The patient is a female aged 50–59 · close-up view: 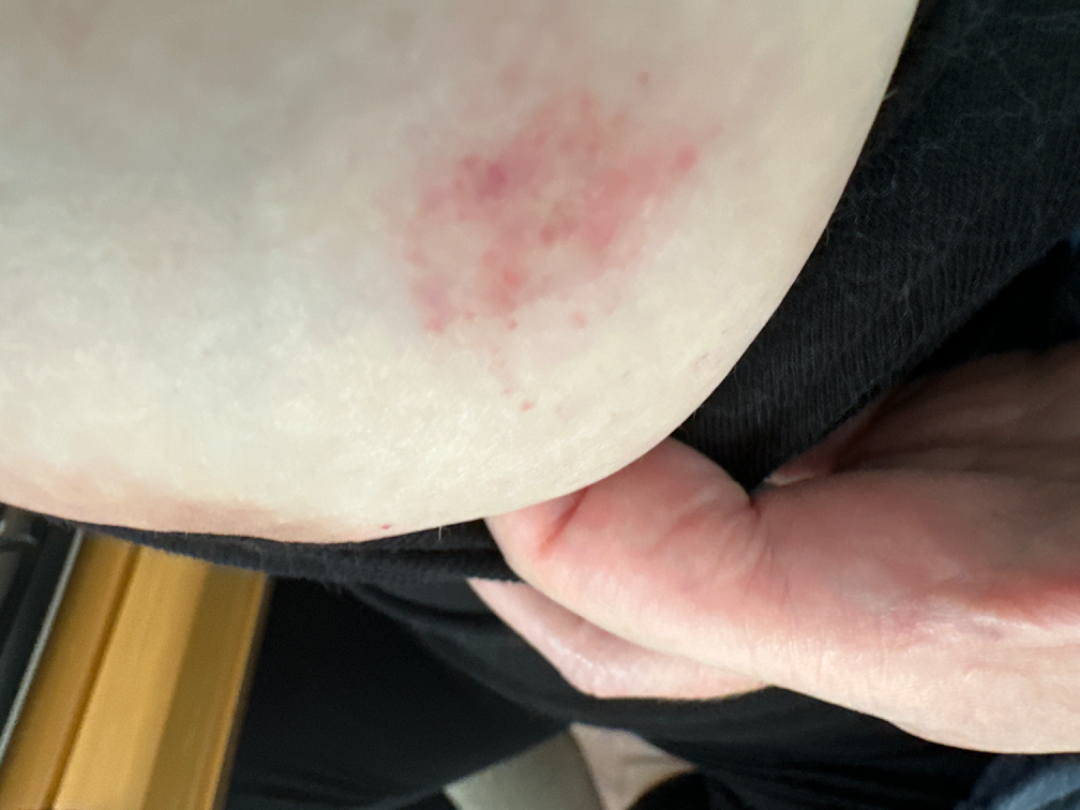Reviewed remotely by one dermatologist: the differential is split between Eczema and Herpes Simplex.